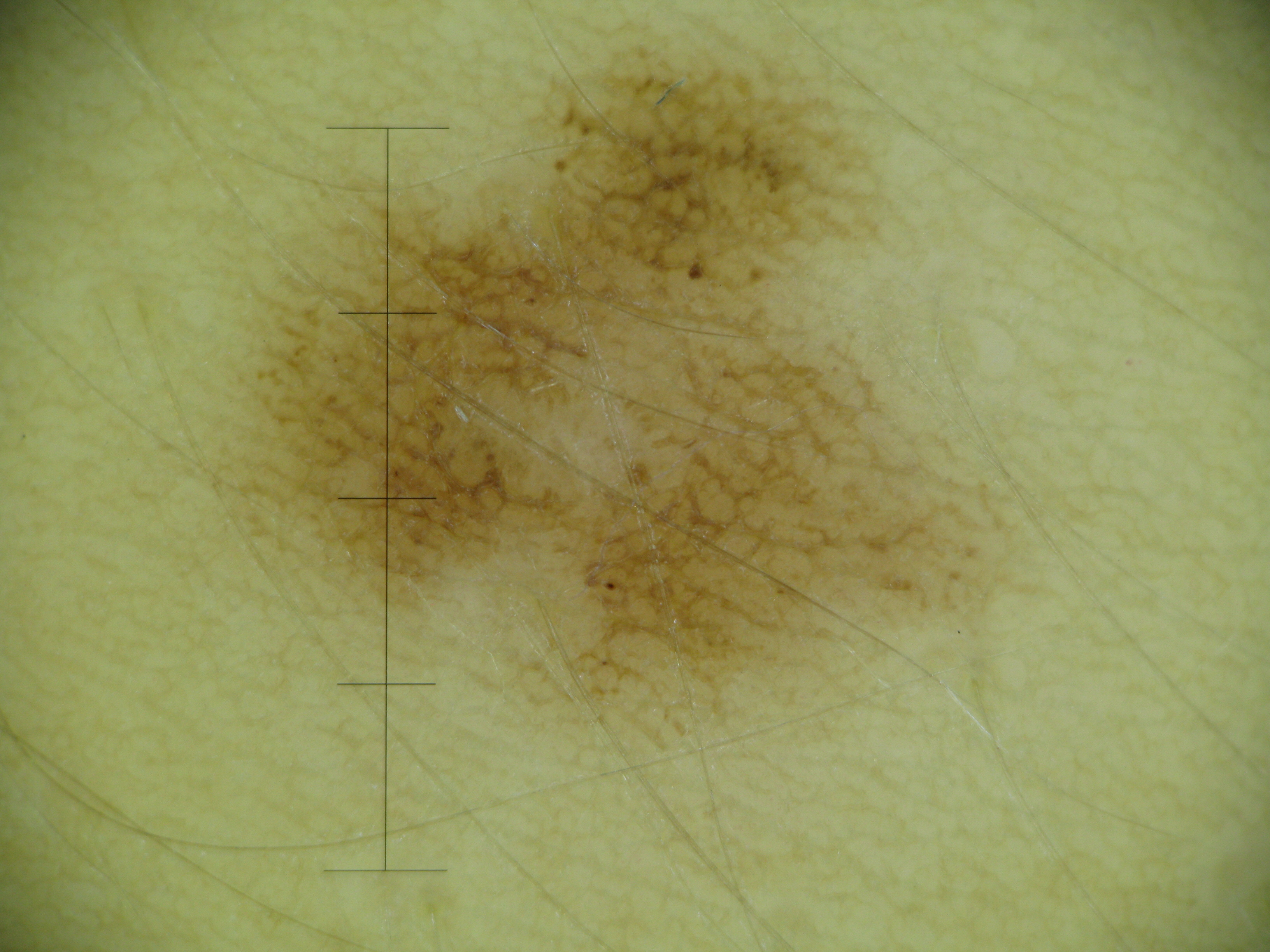A dermoscopic close-up of a skin lesion. Consistent with a dysplastic junctional nevus.